A clinical photograph of a skin lesion — 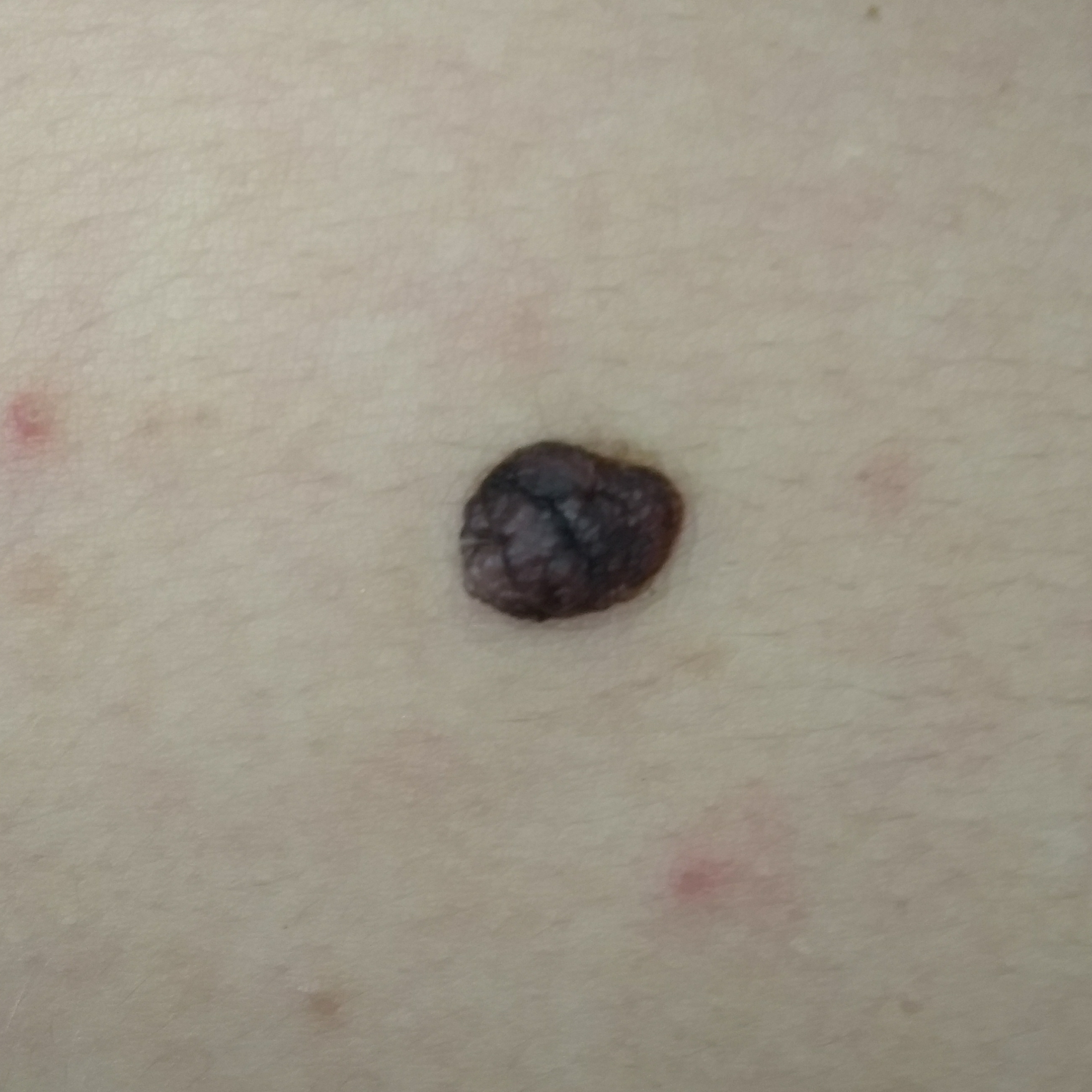By the patient's account, the lesion itches, is elevated, and has grown, but has not bled.
The diagnostic impression was a nevus.